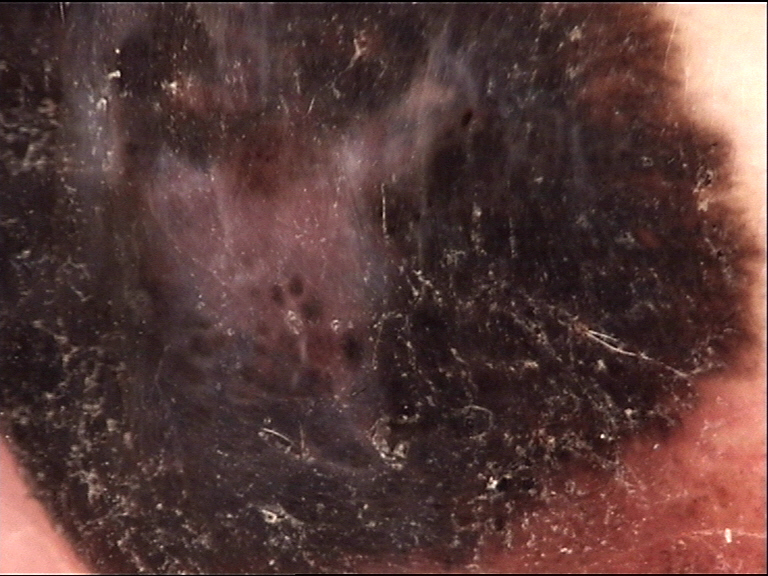Conclusion: The biopsy diagnosis was a melanoma.